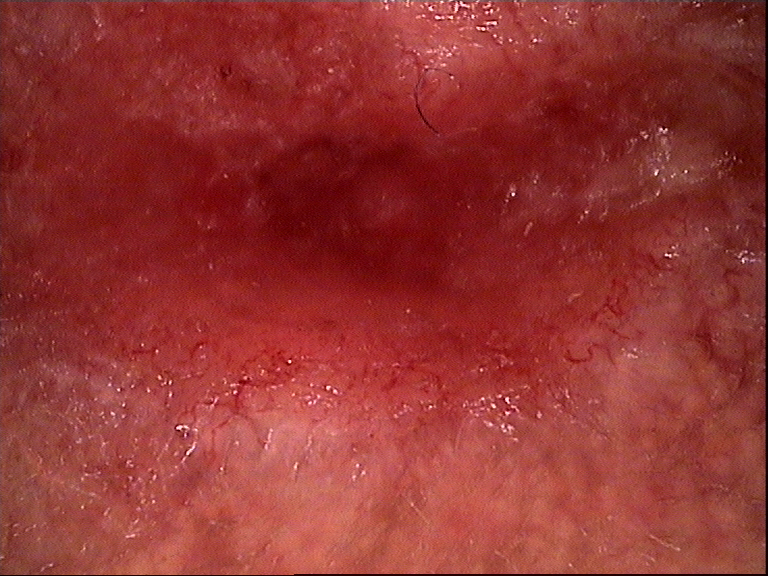<lesion>
<image>dermoscopy</image>
<diagnosis>
<name>squamous cell carcinoma</name>
<code>scc</code>
<malignancy>malignant</malignancy>
<super_class>non-melanocytic</super_class>
<confirmation>histopathology</confirmation>
</diagnosis>
</lesion>